The patient is a female aged 18–29. The palm is involved. Close-up view.
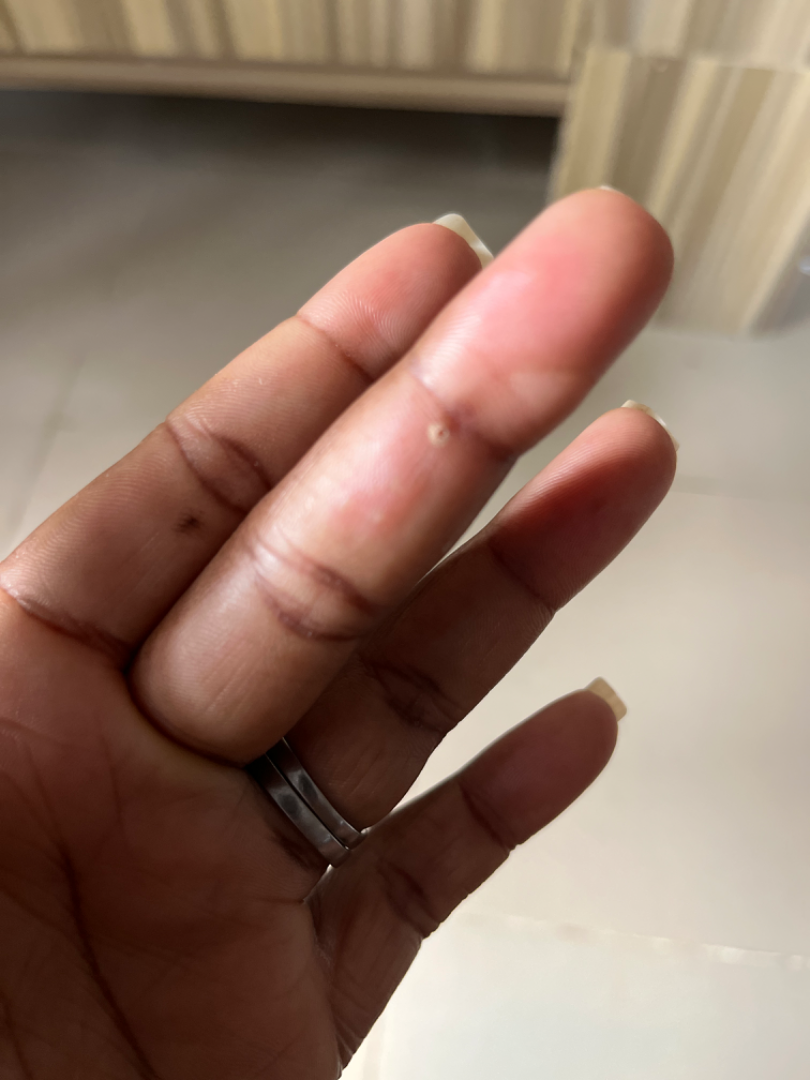assessment = reviewed remotely by one dermatologist: the differential includes Impetigo and Foreign body, with no clear leading consideration.